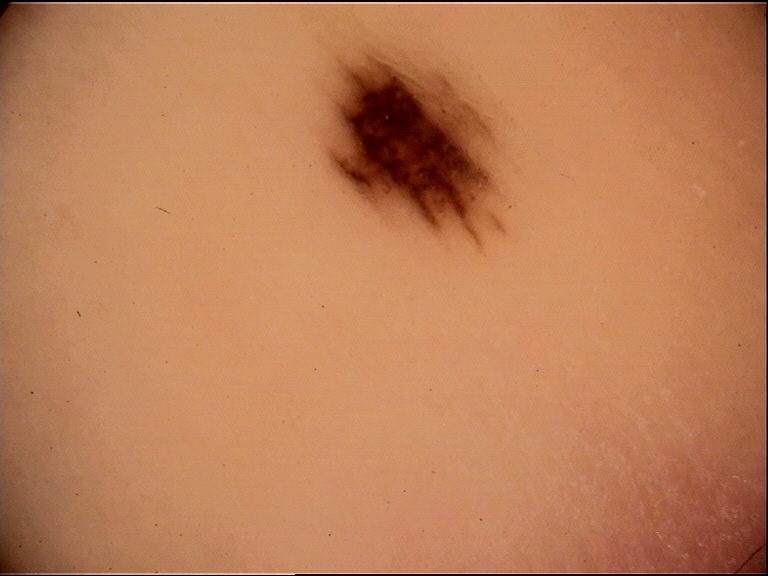assessment = acral junctional nevus (expert consensus).